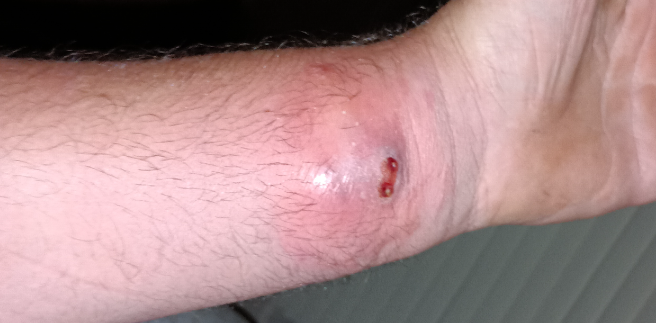• view — at a distance
• lesion texture — raised or bumpy and fluid-filled
• body site — arm
• patient-reported symptoms — bleeding, itching, burning, darkening, enlargement and pain
• skin tone — Fitzpatrick skin type III; human graders estimated MST 2
• subject — male, age 40–49
• impression — most consistent with Abscess; less probable is Insect Bite; less likely is Sweet syndrome; a more distant consideration is Pyoderma Gangrenosum; lower on the differential is Skin and soft tissue atypical mycobacterial infection; a remote consideration is Snake bite - wound